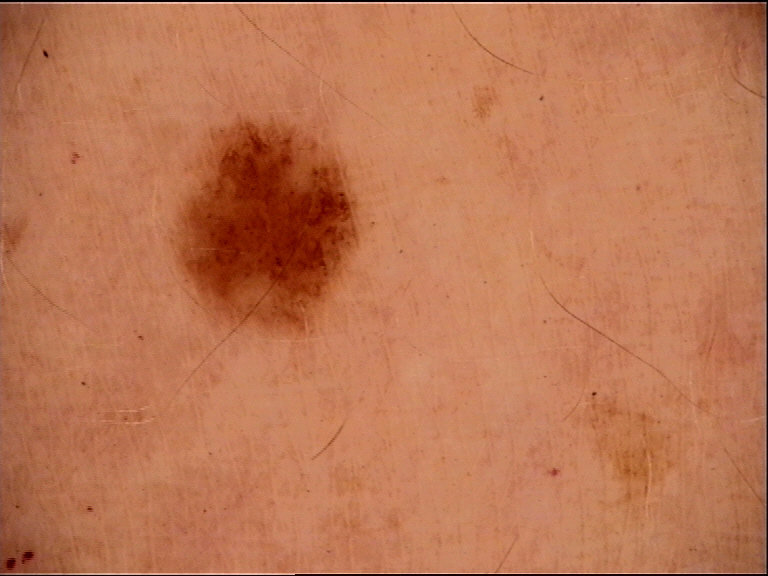The diagnosis was a dysplastic junctional nevus.